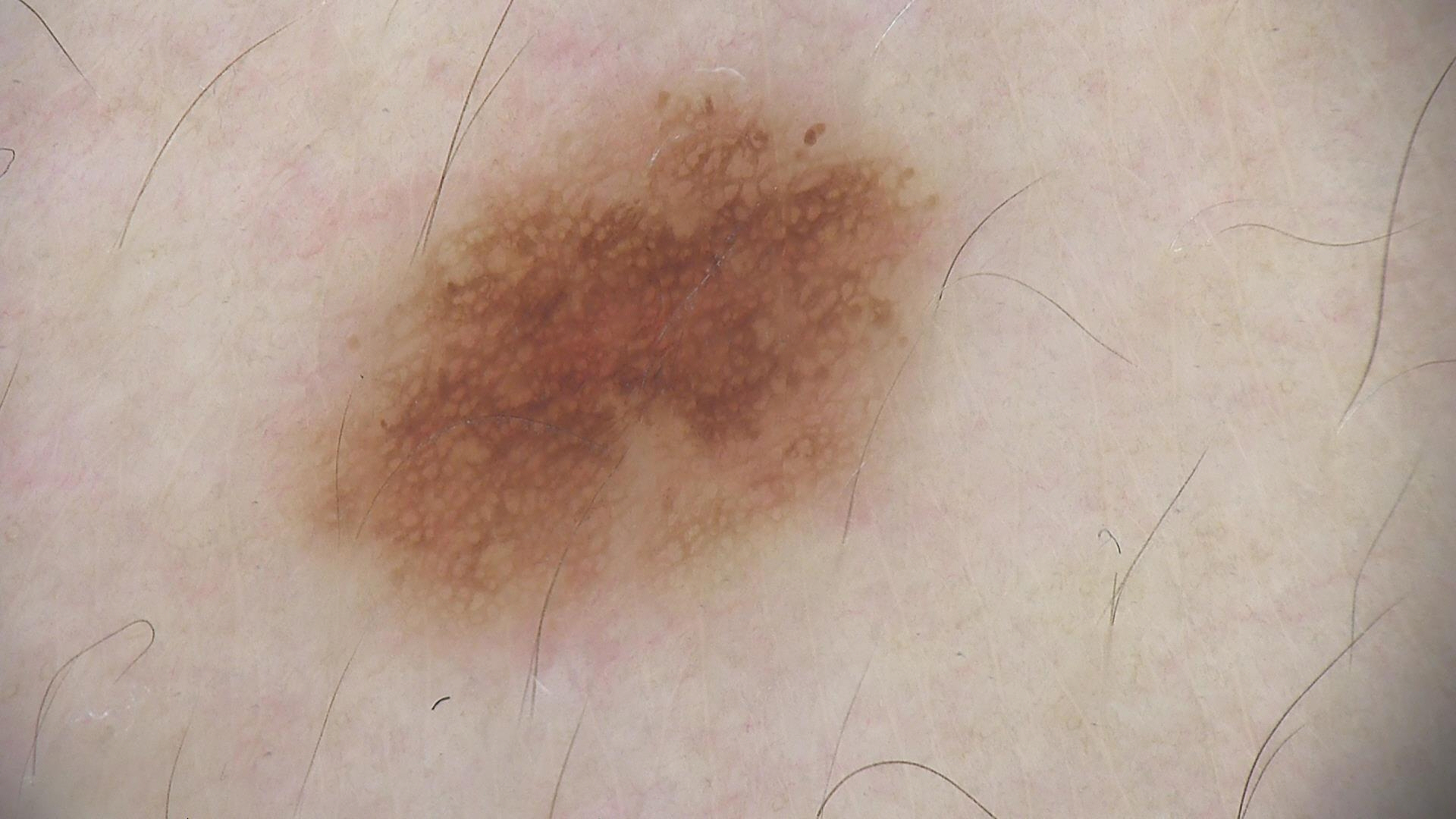Q: What is the diagnosis?
A: dysplastic junctional nevus (expert consensus)